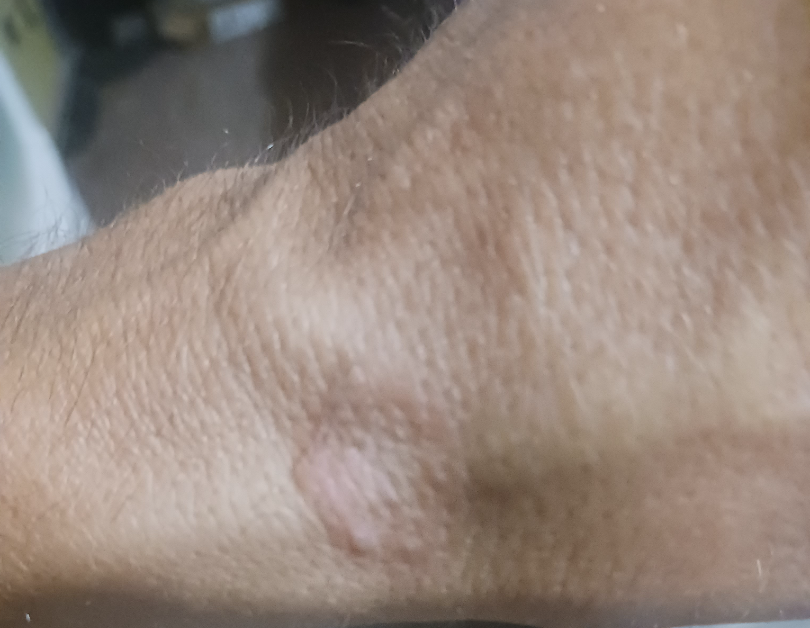| key | value |
|---|---|
| differential diagnosis | Granuloma annulare (favored) |